A dermoscopic image of a skin lesion. A female patient approximately 45 years of age: 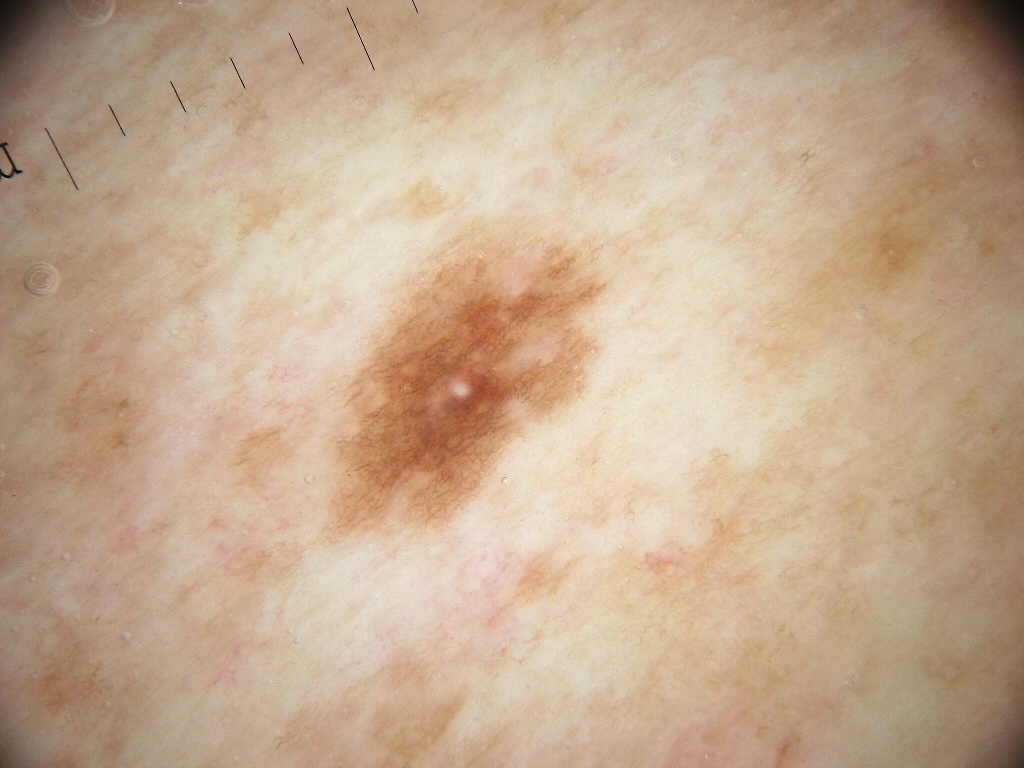In (x1, y1, x2, y2) order, the lesion is located at 329, 245, 599, 532. Dermoscopic examination shows pigment network and milia-like cysts. Consistent with a melanocytic nevus.